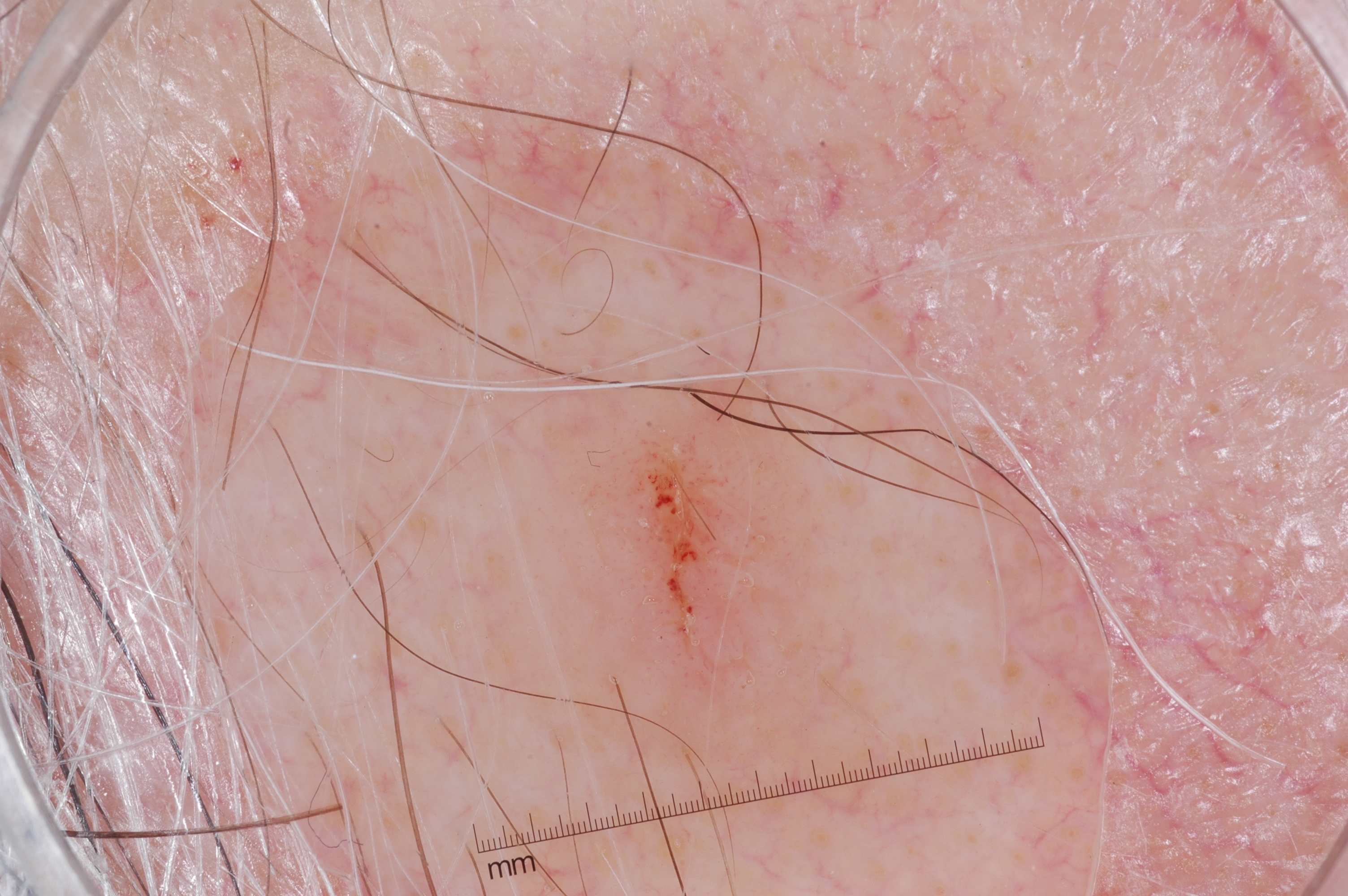image = dermatoscopic image of a skin lesion | lesion bbox = left=543, top=373, right=840, bottom=727 | impression = a seborrheic keratosis.